Reported duration is about one day. The lesion is associated with enlargement and itching. The lesion involves the arm. The photograph was taken at an angle. The patient considered this a rash. The lesion is described as raised or bumpy:
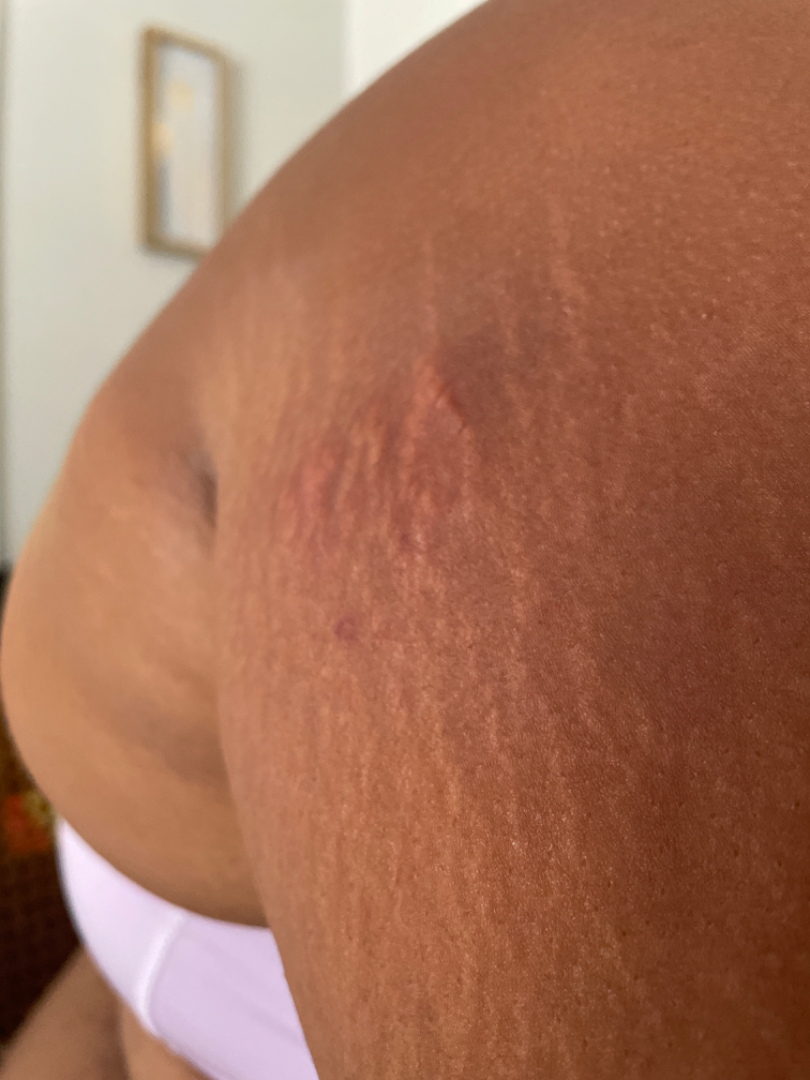The case was difficult to assess from the available photograph.